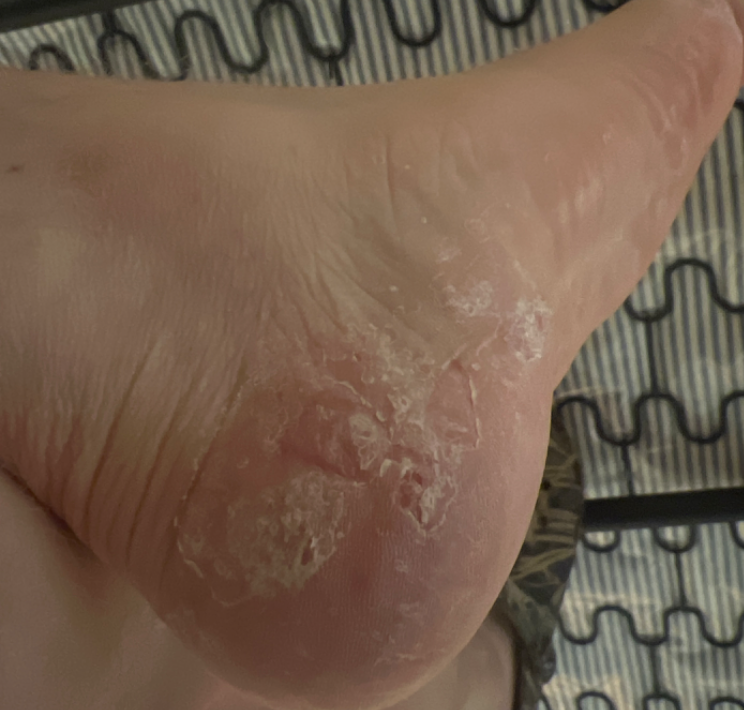Findings:
The skin condition could not be confidently assessed from this image.
Background:
The contributor is 18–29, male. The photograph was taken at an angle. The patient reports the lesion is rough or flaky and fluid-filled. Present for three to twelve months. The patient reports associated fatigue, shortness of breath and joint pain. The lesion is associated with itching, bleeding, burning and pain. Located on the top or side of the foot and sole of the foot. Skin tone: human graders estimated Monk Skin Tone 1–2.